A female subject aged approximately 75; a dermoscopic image of a skin lesion.
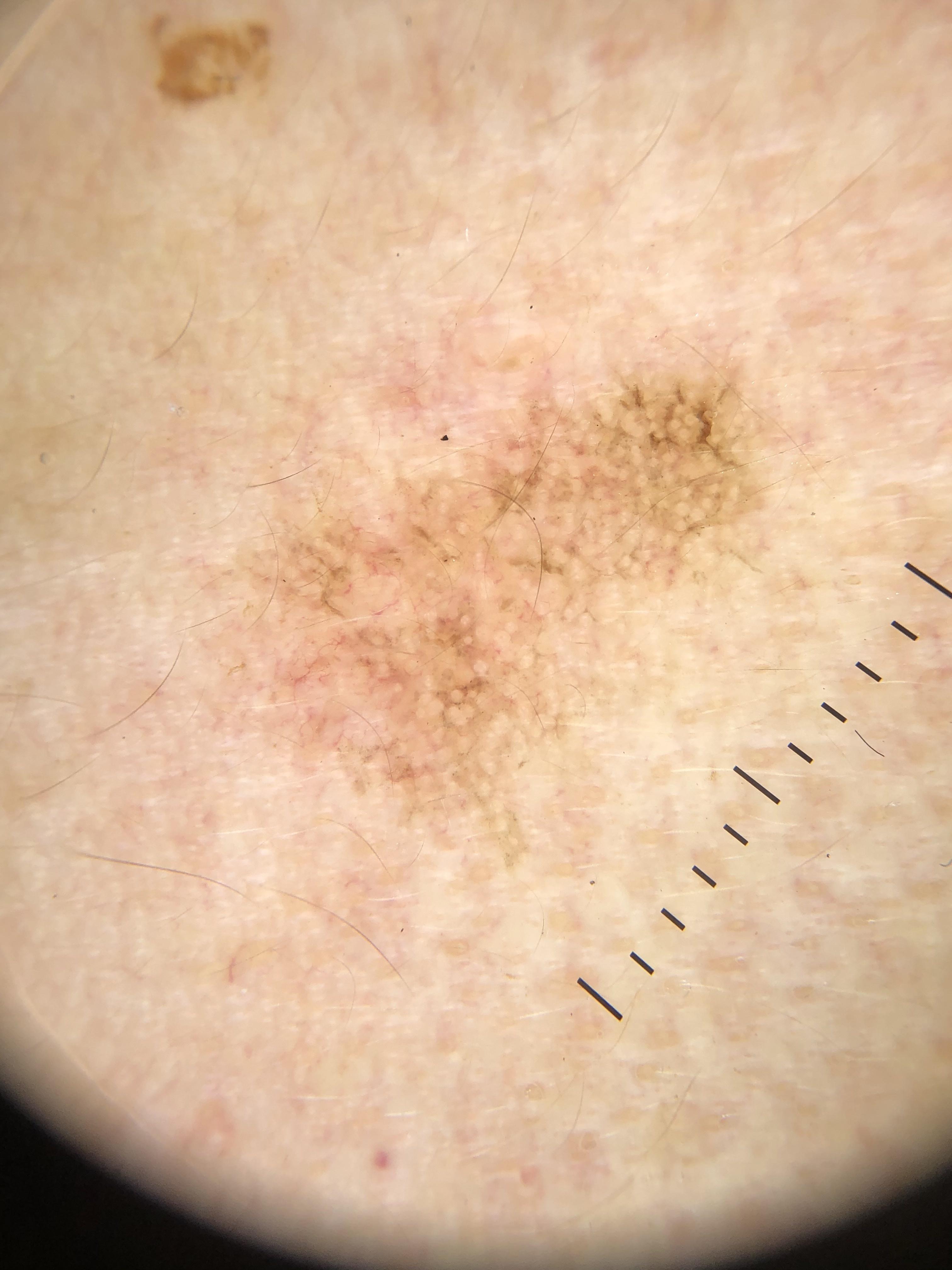Q: Where on the body is the lesion?
A: the head or neck
Q: What is this lesion?
A: Solar or actinic keratosis (biopsy-proven)